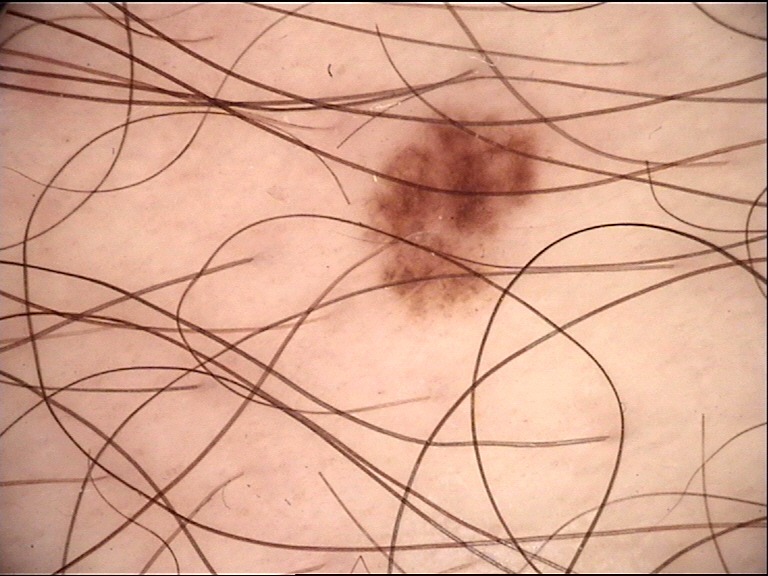modality = dermatoscopy | lesion type = banal | class = junctional nevus (expert consensus).